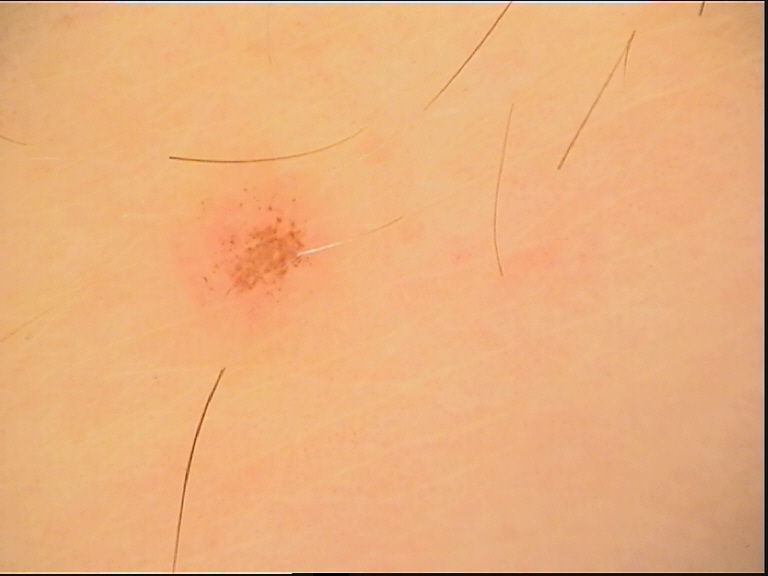Q: What was the diagnostic impression?
A: dysplastic junctional nevus (expert consensus)